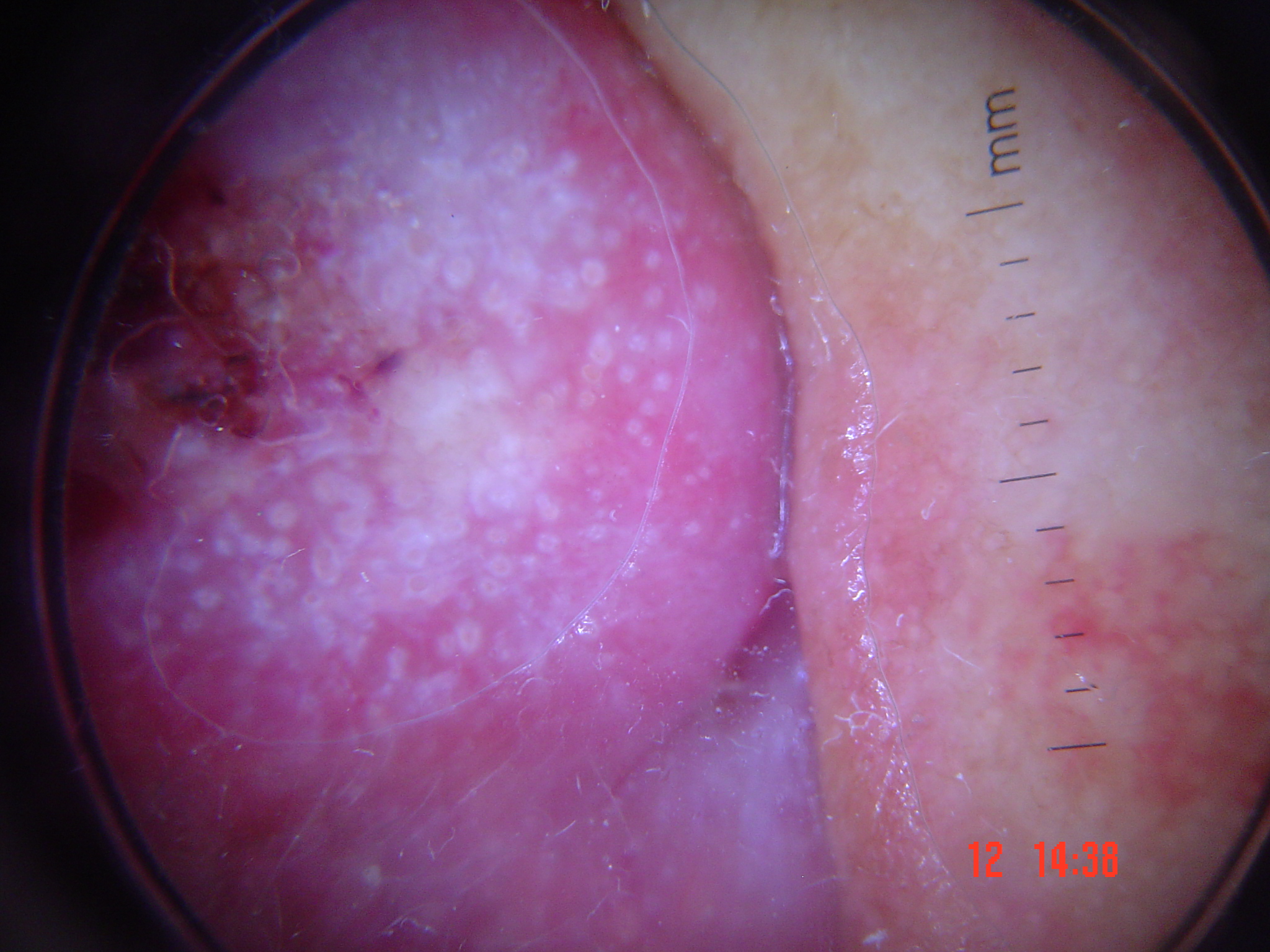modality = dermoscopy
category = keratinocytic
class = squamous cell carcinoma (biopsy-proven)